A skin lesion imaged with contact-polarized dermoscopy. A male subject about 65 years old — 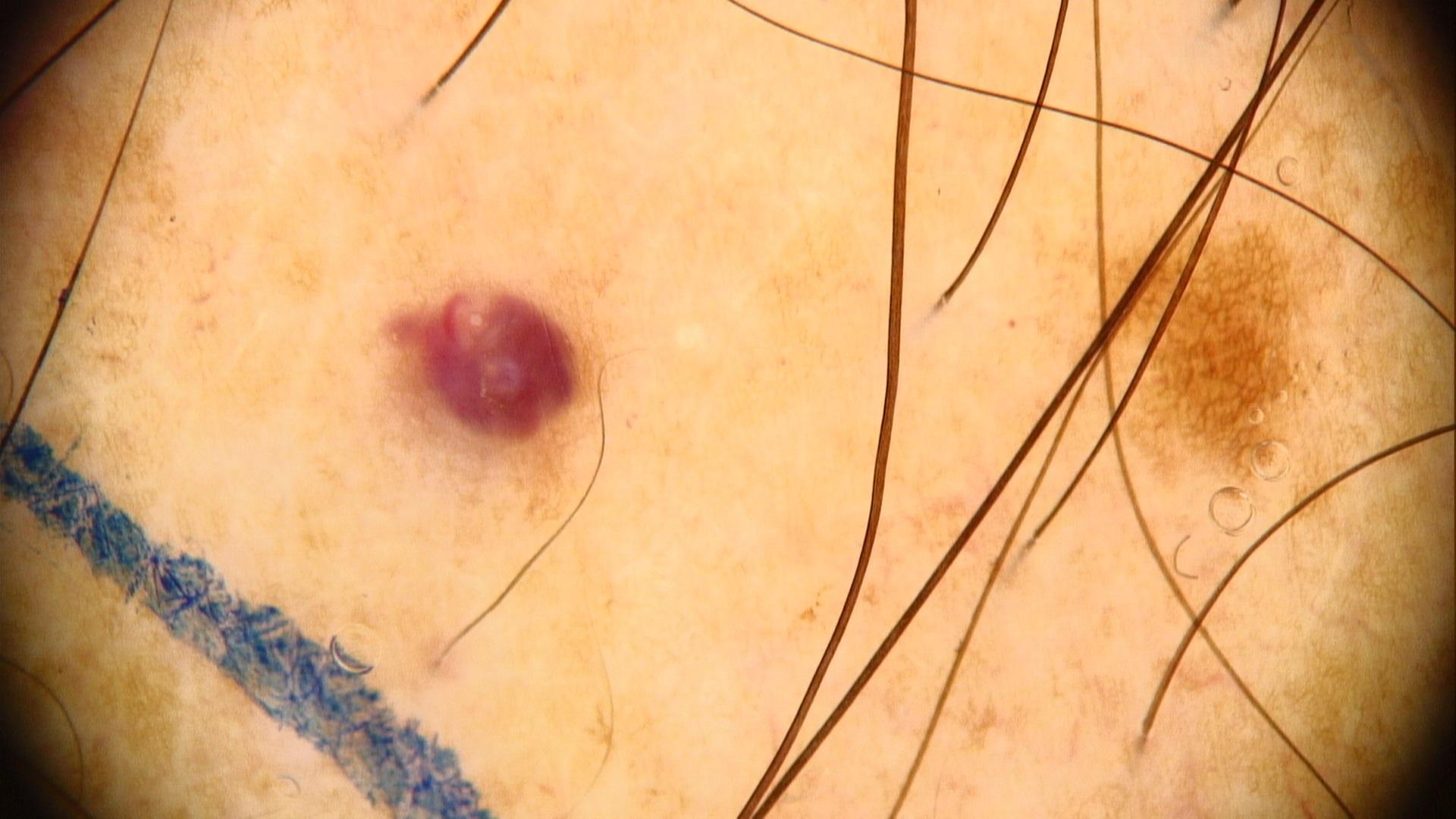Located on the trunk. The clinical impression was a benign vascular lesion.